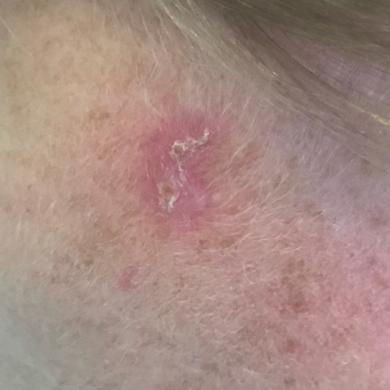A clinical photo of a skin lesion taken with a smartphone.
The lesion is on the face.
The patient describes that the lesion itches, but has not bled and does not hurt.
The consensus clinical diagnosis was an actinic keratosis.